Texture is reported as raised or bumpy · close-up view · the lesion involves the leg · self-categorized by the patient as acne · the condition has been present for less than one week:
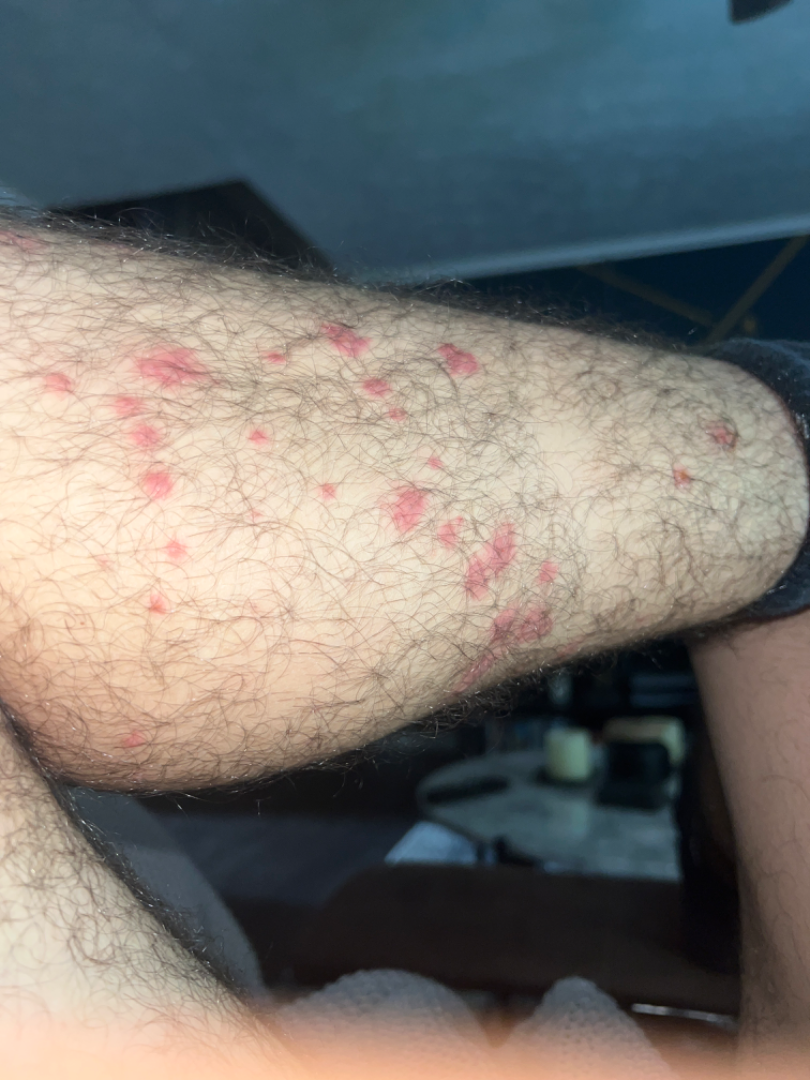impression — consistent with Insect Bite.